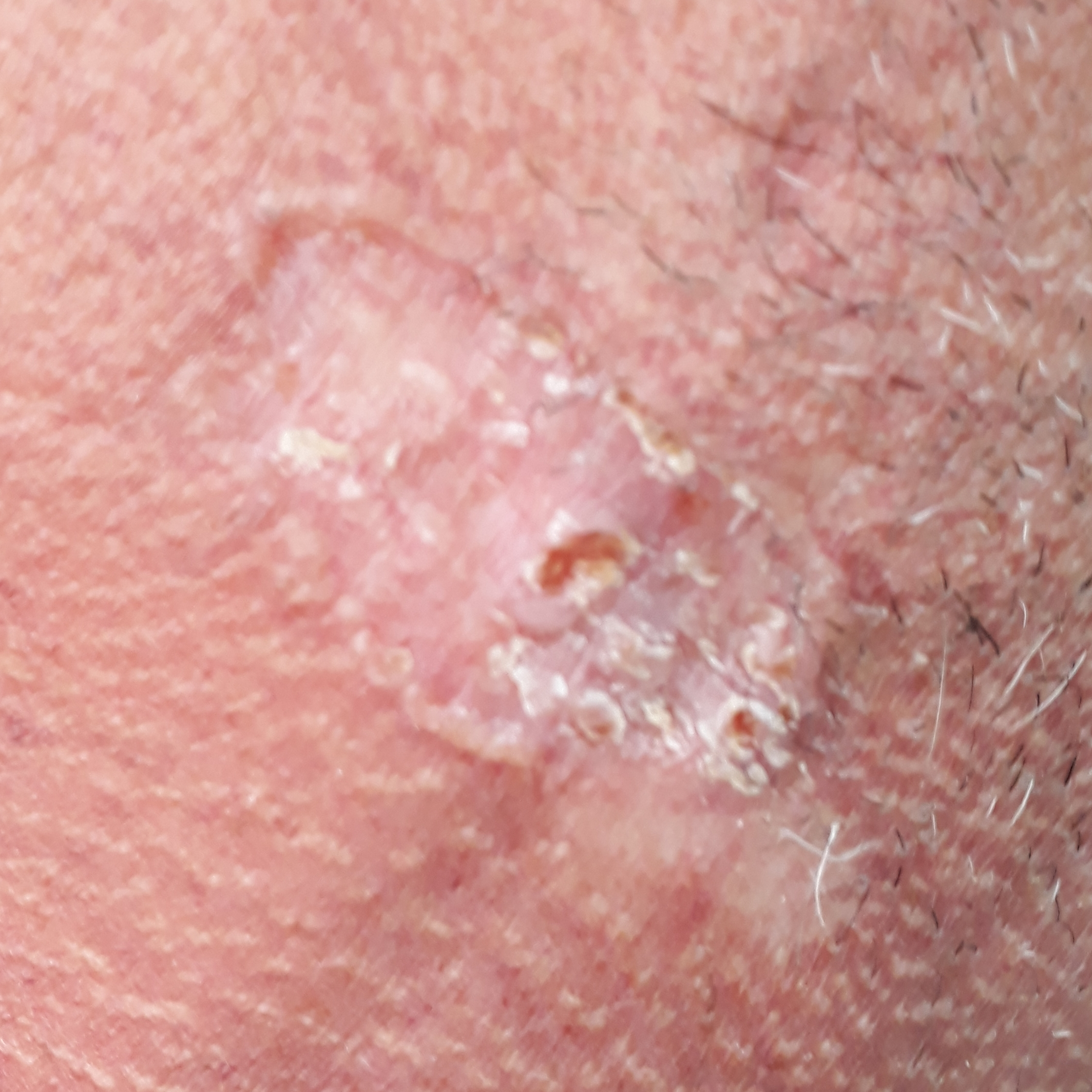{
  "patient": {
    "age": 51,
    "gender": "male"
  },
  "risk_factors": {
    "positive": [
      "smoking",
      "pesticide exposure"
    ]
  },
  "image": "clinical photograph",
  "lesion_size": {
    "diameter_1_mm": 42.0,
    "diameter_2_mm": 21.0
  },
  "symptoms": {
    "present": [
      "itching",
      "growth",
      "elevation",
      "bleeding"
    ]
  },
  "diagnosis": {
    "name": "basal cell carcinoma",
    "code": "BCC",
    "malignancy": "malignant",
    "confirmation": "histopathology"
  }
}